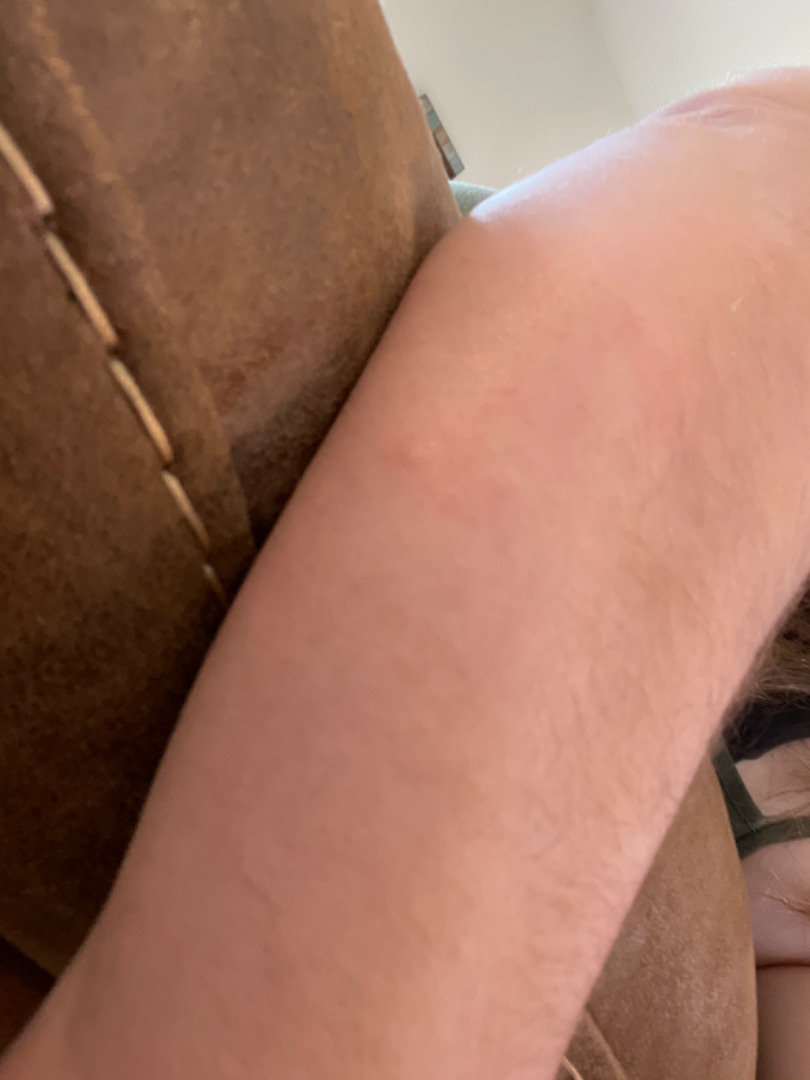Case summary:
- assessment · the leading consideration is Insect Bite; an alternative is Allergic Contact Dermatitis; less probable is Scabies